Dermoscopy of a skin lesion.
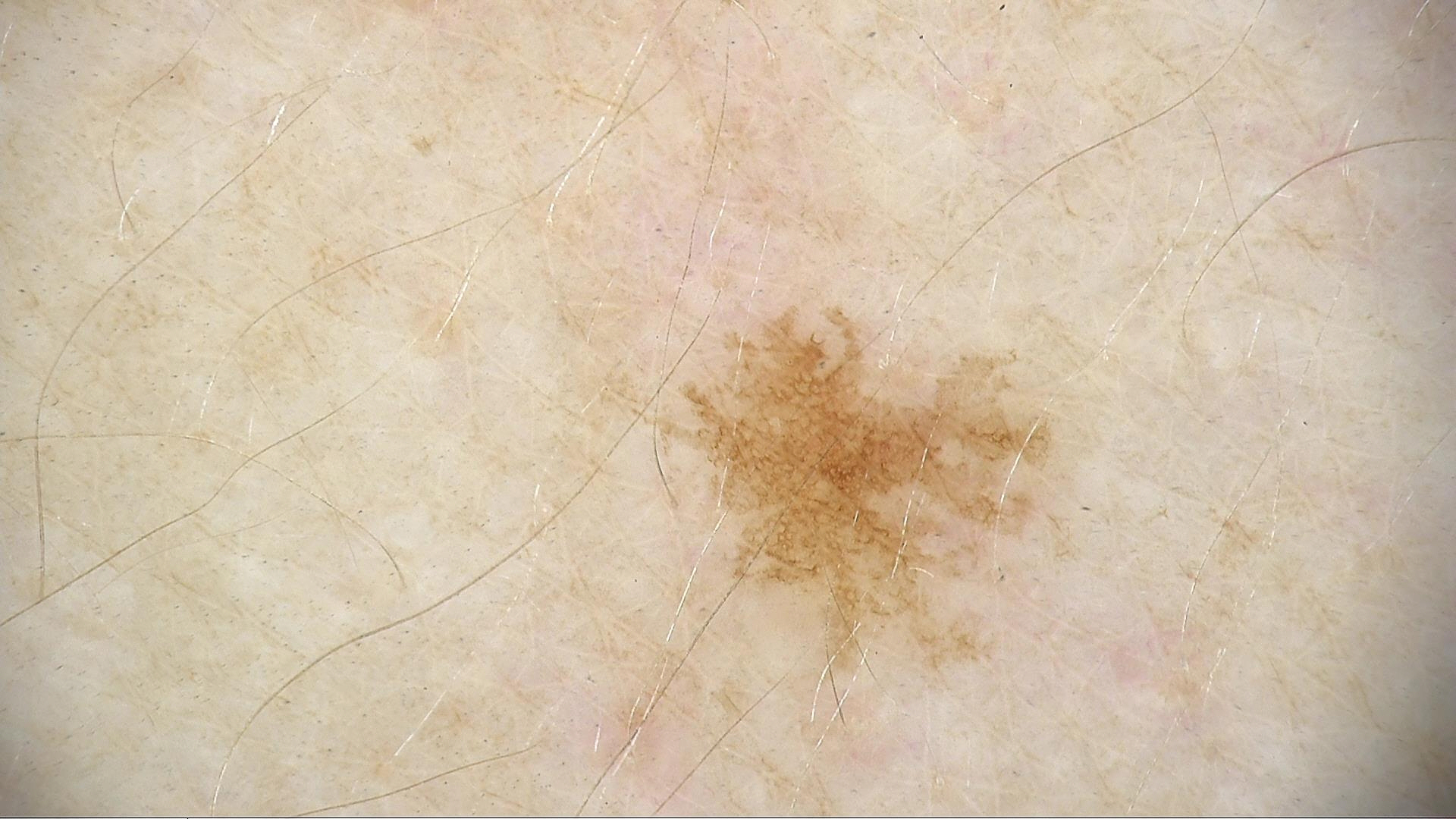assessment=solar lentigo (expert consensus).